A dermoscopic close-up of a skin lesion:
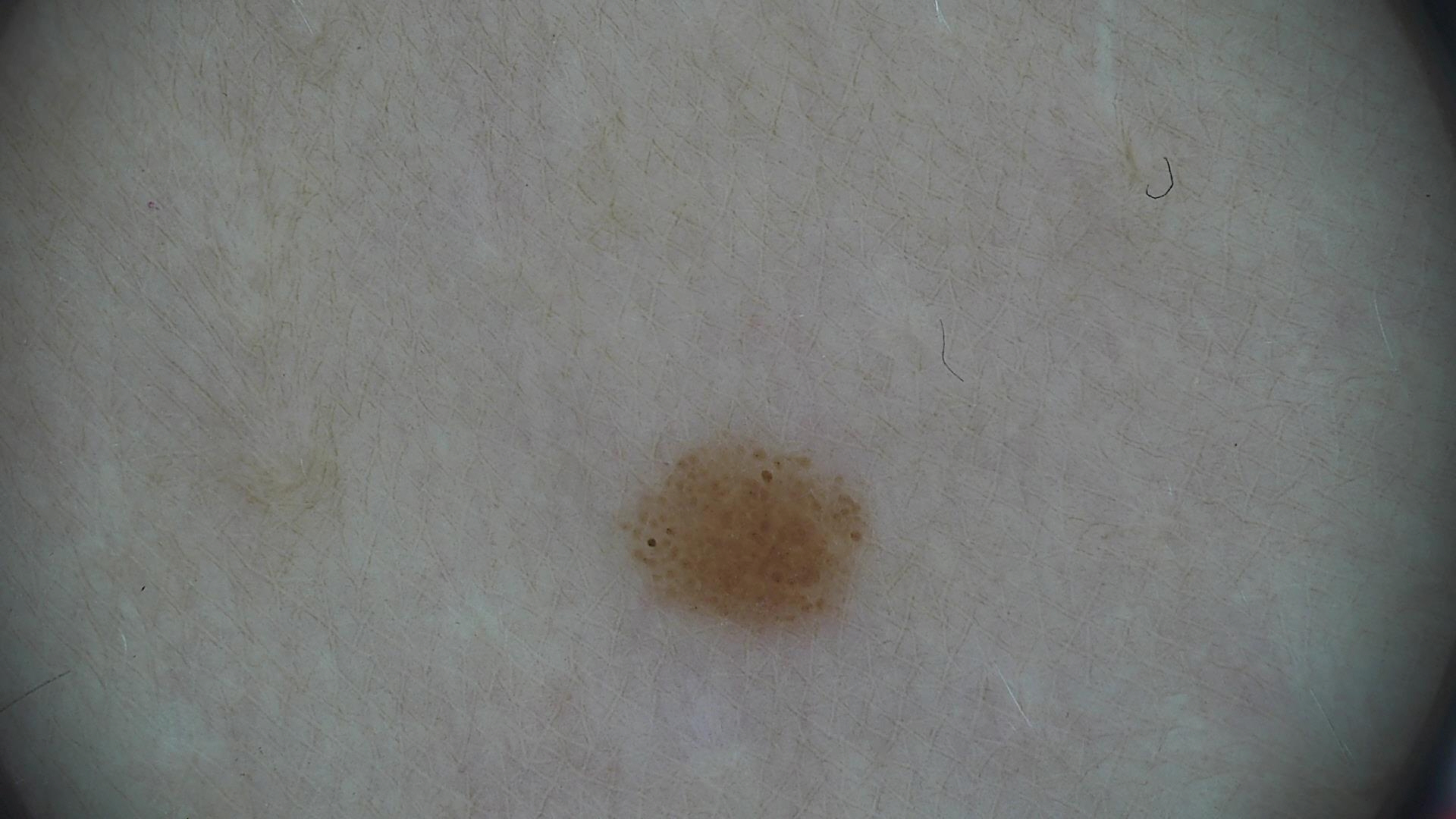The diagnostic label was a benign lesion — a dysplastic junctional nevus.